Dermoscopy of a skin lesion.
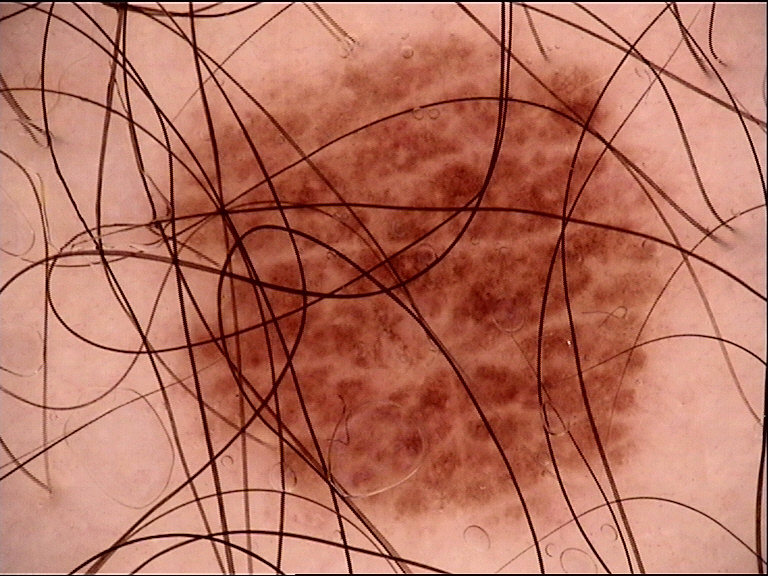Case:
– diagnosis: dysplastic junctional nevus (expert consensus)